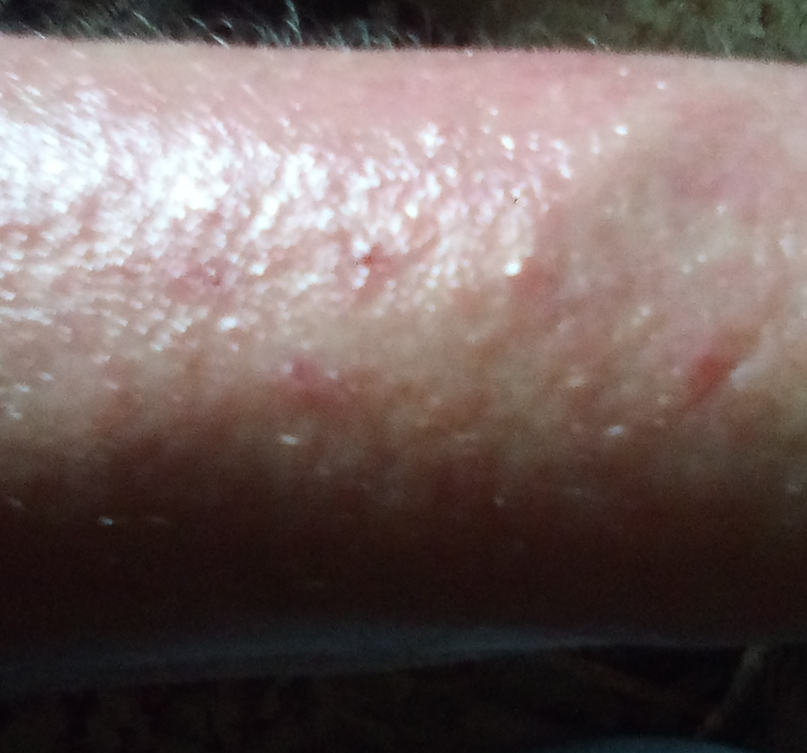Review:
The reviewing dermatologist was unable to assign a differential diagnosis from the image.
Patient information:
Female subject, age 50–59. The lesion involves the arm. The patient considered this a rash. No associated systemic symptoms reported. This is a close-up image. Skin tone: self-reported FST III; lay reviewers estimated a Monk Skin Tone of 2. The lesion is described as rough or flaky, fluid-filled and raised or bumpy. Reported lesion symptoms include itching. The contributor notes the condition has been present for one to four weeks.